The chart notes prior skin cancer (patient or family), pesticide exposure, and alcohol use; the patient is skin type II; a male patient 60 years old; a clinical photo of a skin lesion taken with a smartphone:
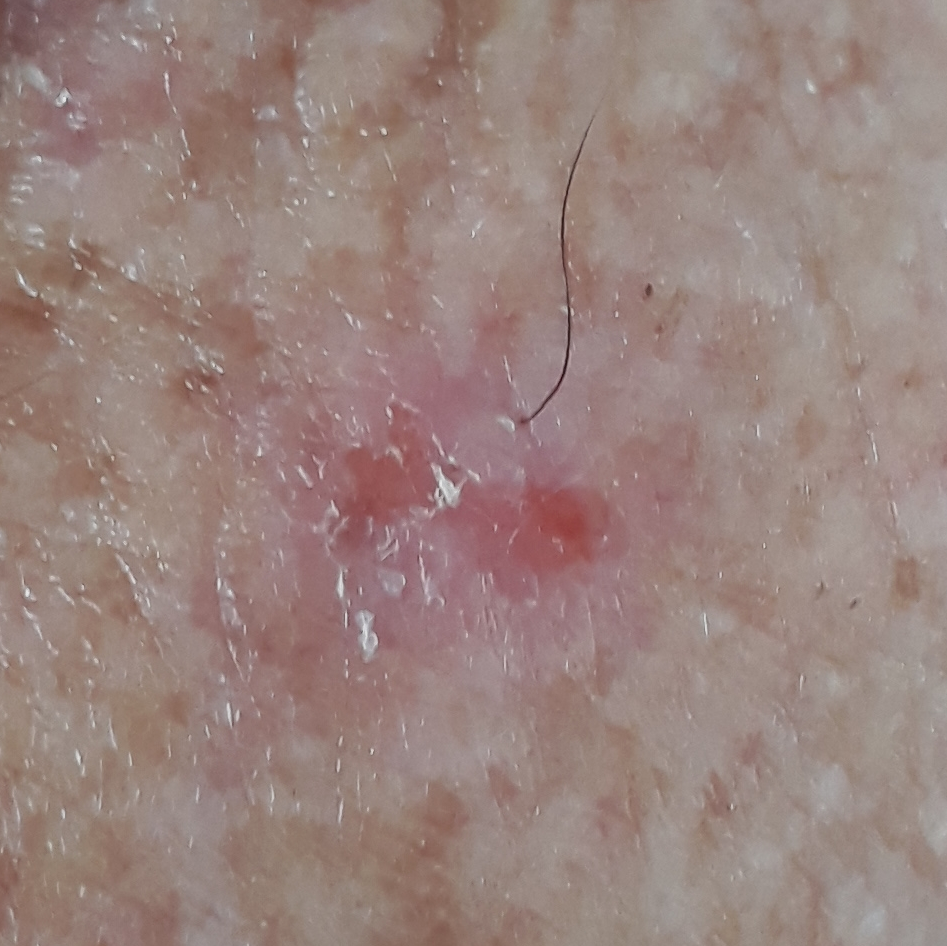The lesion involves the chest.
The lesion measures 8 × 6 mm.
The biopsy diagnosis was a basal cell carcinoma.